A male subject roughly 80 years of age. A dermatoscopic image of a skin lesion — 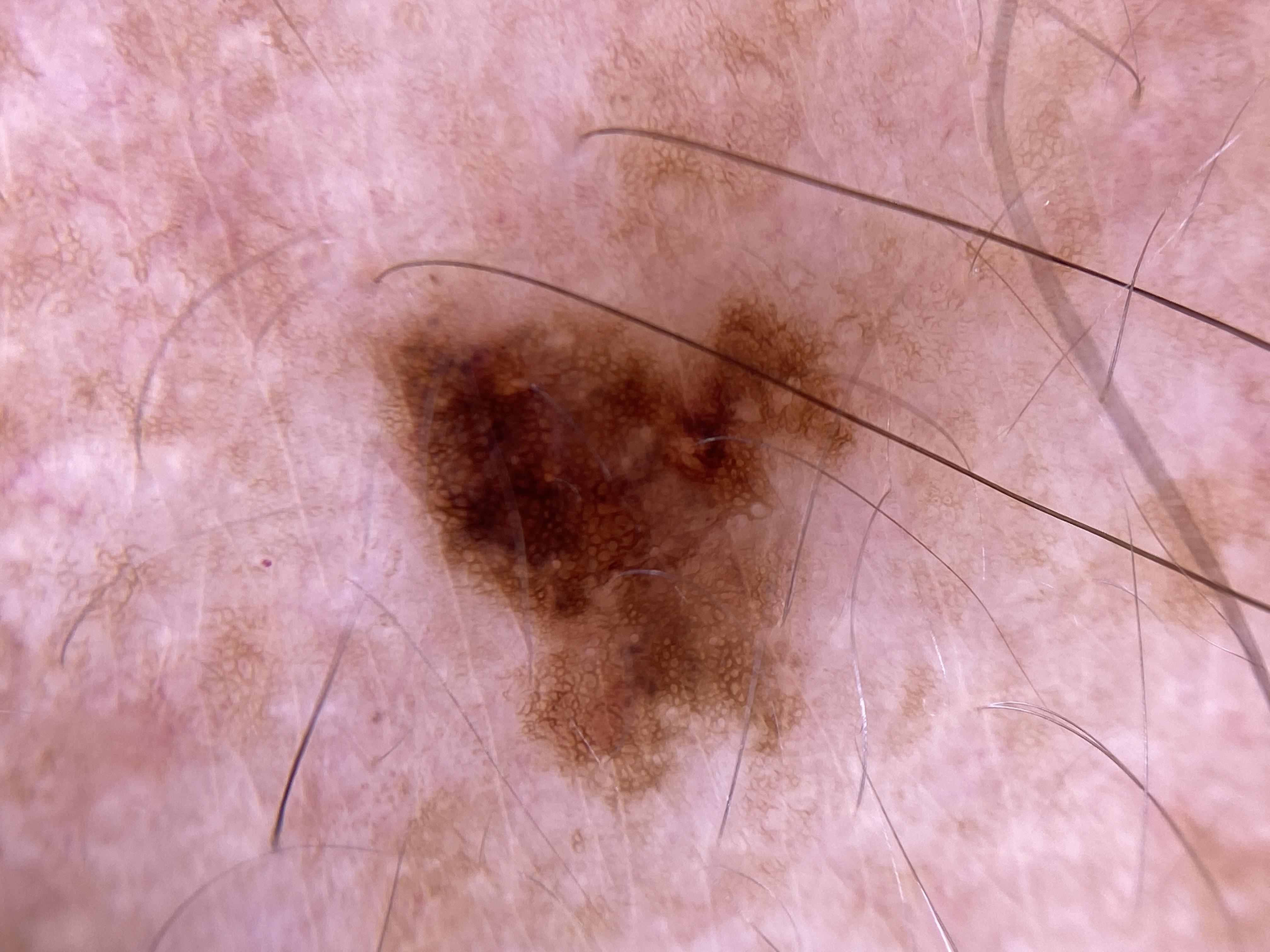The lesion is located on the trunk.
The biopsy diagnosis was a nevus.